Skin tone: lay graders estimated Monk skin tone scale 1–2, this image was taken at a distance: 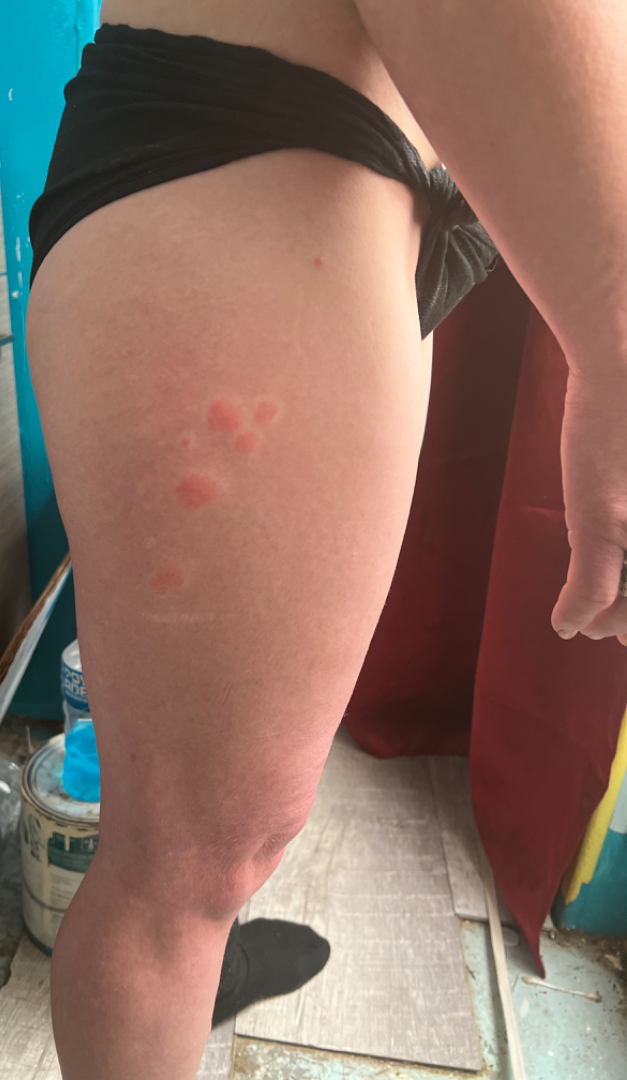On photographic review, Insect Bite and Eczema were considered with similar weight.